This is a close-up image: 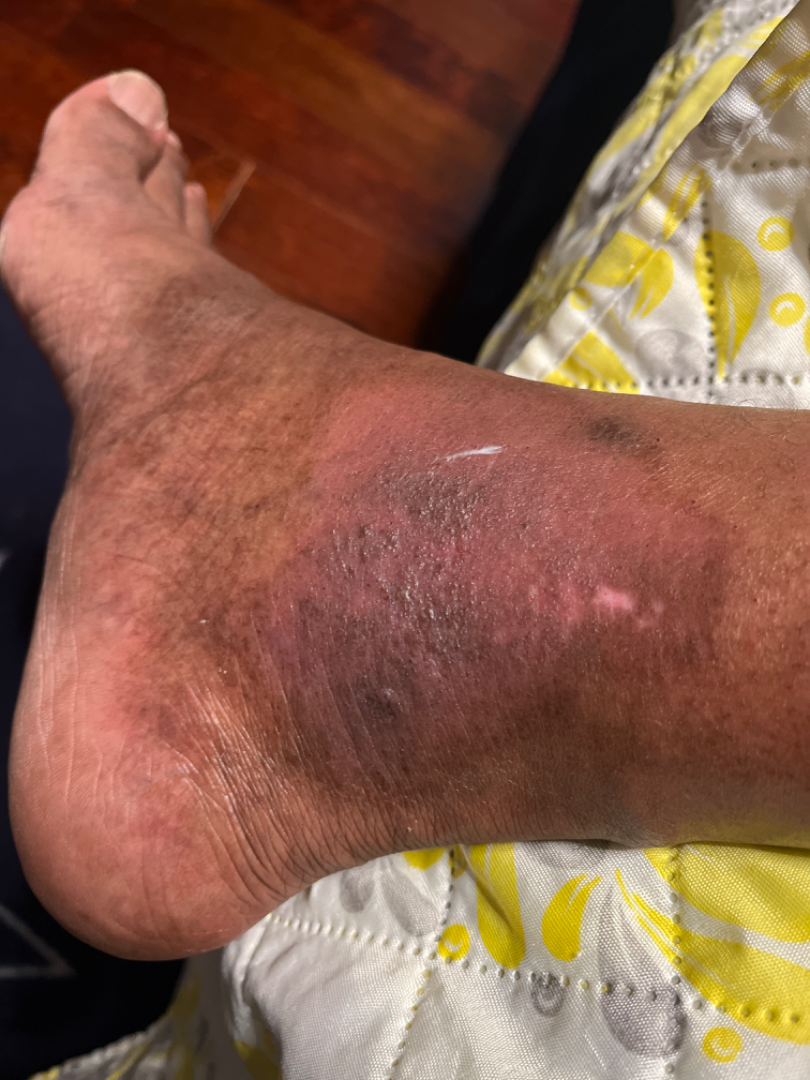Review:
A single dermatologist reviewed the case: the differential, in no particular order, includes Tinea, Stasis Dermatitis and Lichen Simplex Chronicus.